A dermoscopic close-up of a skin lesion.
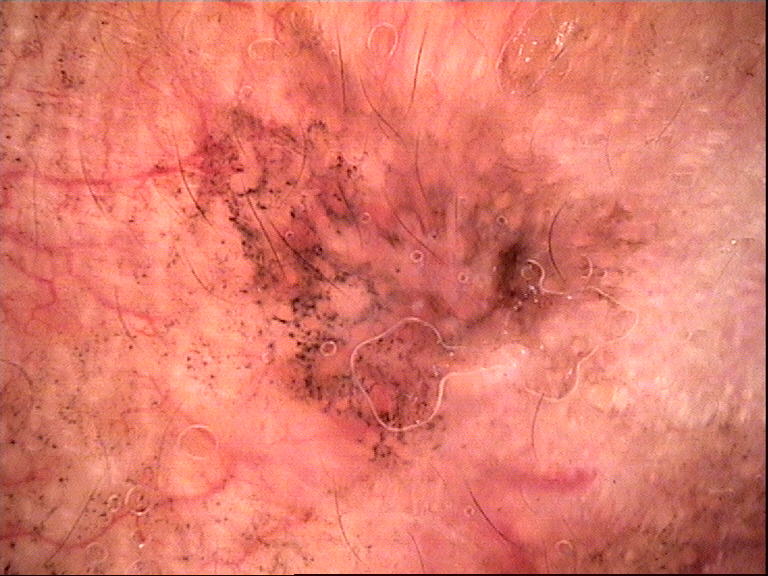This is a keratinocytic lesion. The diagnostic label was a lichenoid keratosis.